The contributor is 40–49, female. Located on the arm. A close-up photograph:
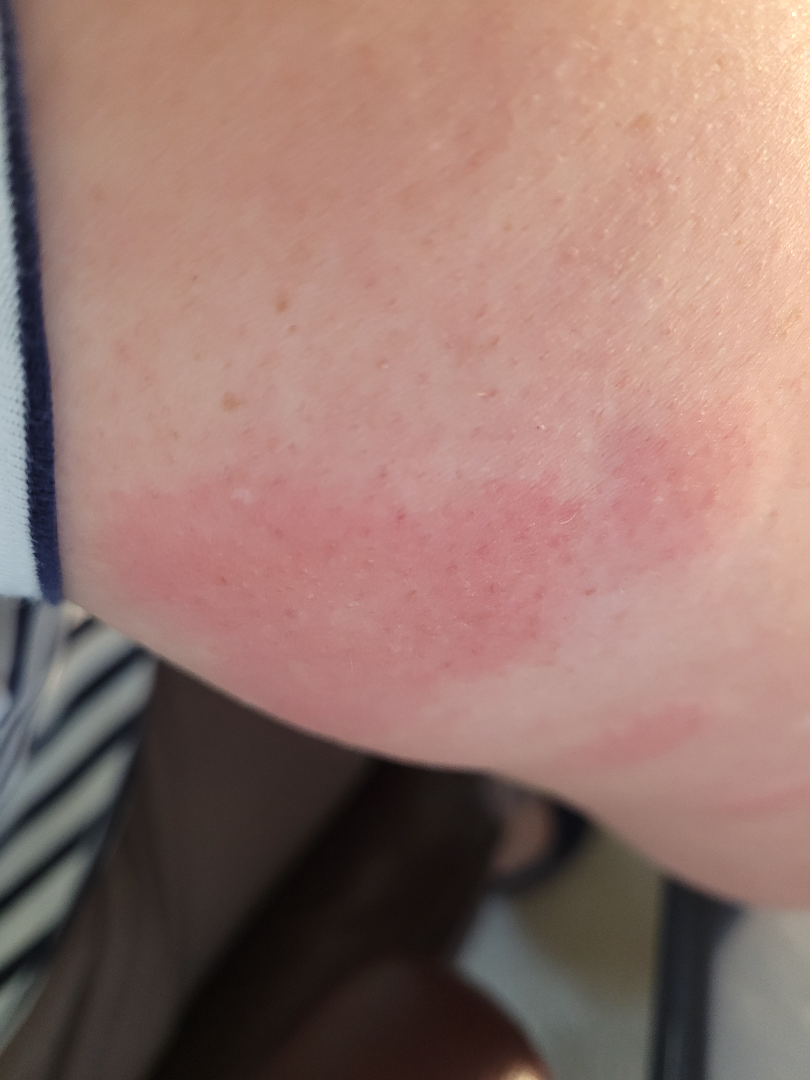differential diagnosis — single-reviewer assessment: Urticaria and Allergic Contact Dermatitis were considered with similar weight; a more distant consideration is Panniculitis.